A dermoscopic image of a skin lesion.
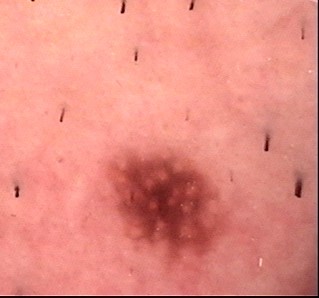{"lesion_type": {"main_class": "banal", "pattern": "compound"}, "diagnosis": {"name": "Miescher nevus", "code": "mcb", "malignancy": "benign", "super_class": "melanocytic", "confirmation": "expert consensus"}}